Dermoscopy of a skin lesion: 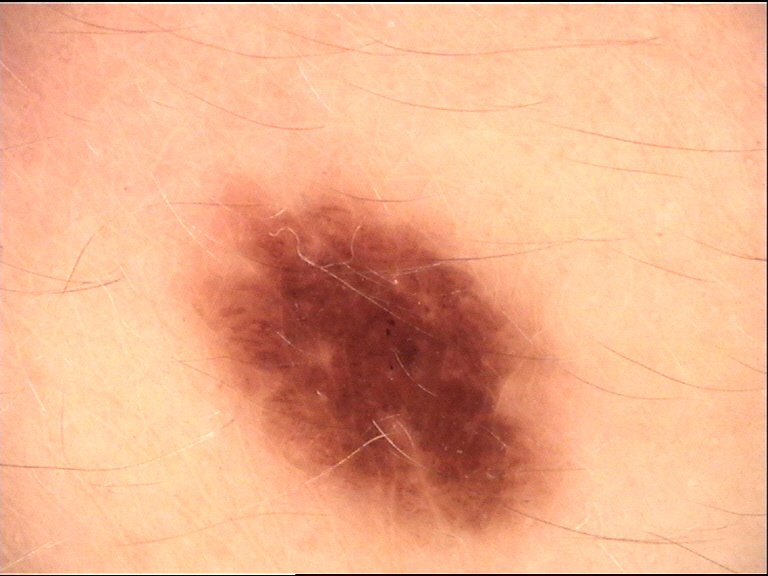{"diagnosis": {"name": "dysplastic junctional nevus", "code": "jd", "malignancy": "benign", "super_class": "melanocytic", "confirmation": "expert consensus"}}